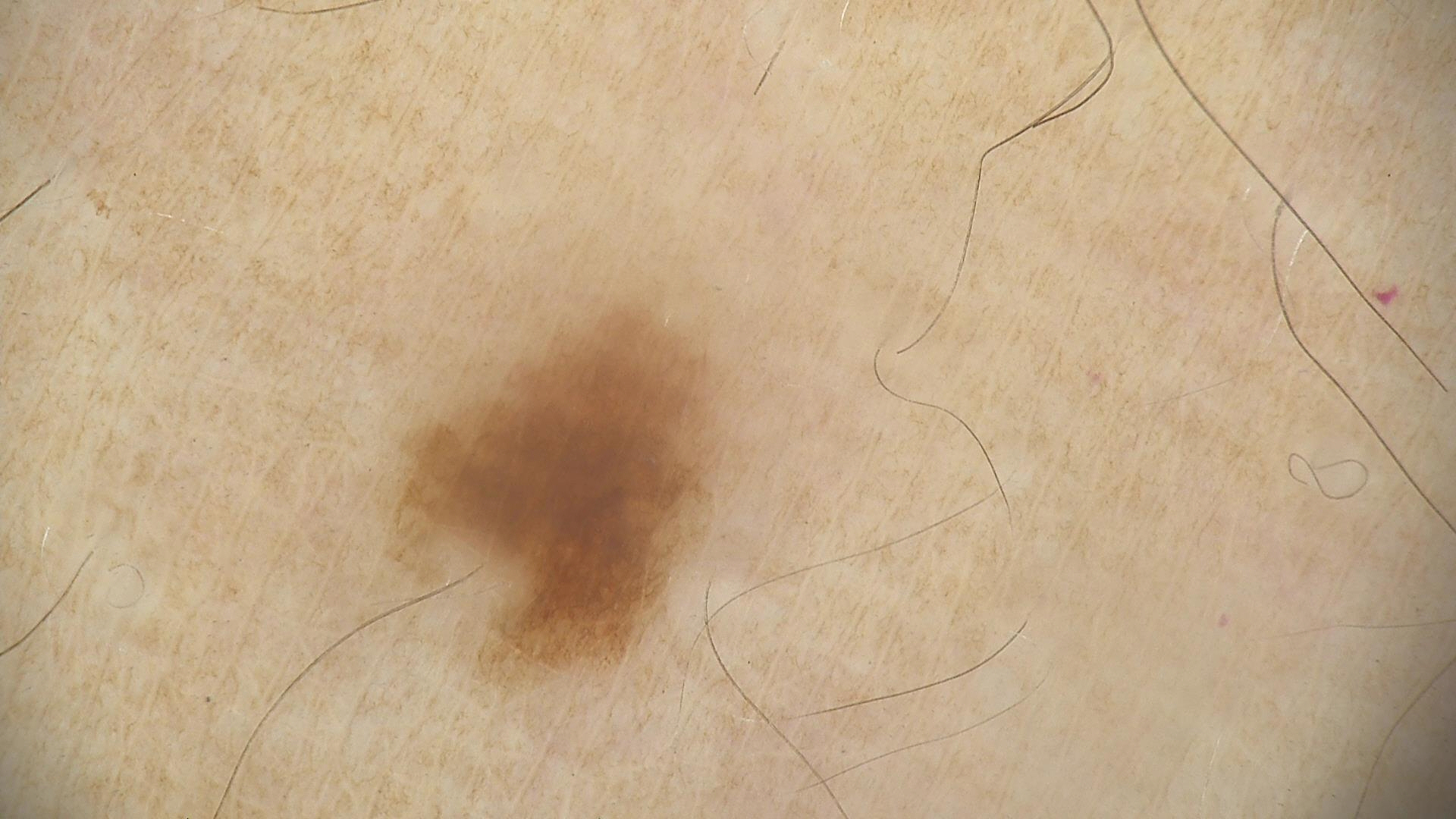Findings: Dermoscopy of a skin lesion. Conclusion: The diagnostic label was a benign lesion — a dysplastic junctional nevus.